Located on the back of the hand and palm. The lesion is described as rough or flaky and raised or bumpy. The contributor reports bothersome appearance, itching and enlargement. The subject is a female aged 50–59. No relevant systemic symptoms. The photo was captured at an angle. The patient described the issue as a rash. Present for more than one year:
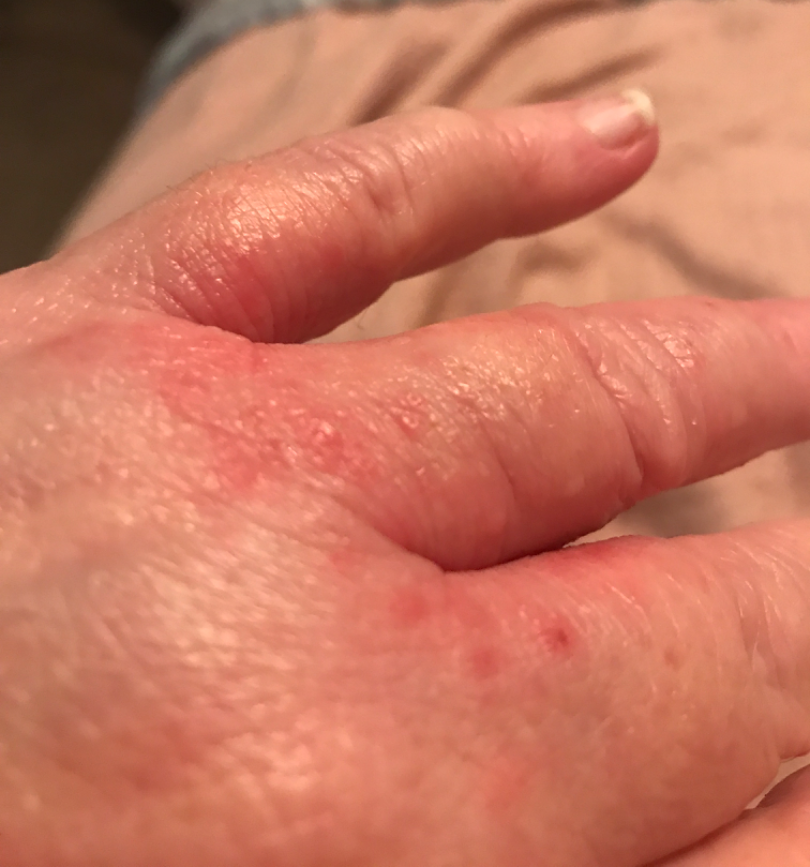Findings:
- differential · favoring Eczema; an alternative is Allergic Contact Dermatitis; a remote consideration is Scabies; less probable is Tinea; less likely is Irritant Contact Dermatitis